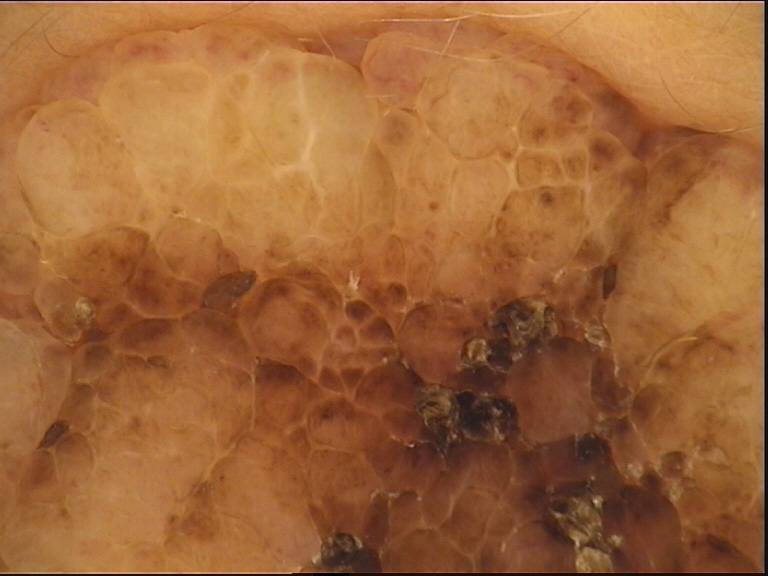| field | value |
|---|---|
| imaging | dermoscopy |
| class | dermal nevus (expert consensus) |